A dermoscopic photograph of a skin lesion:
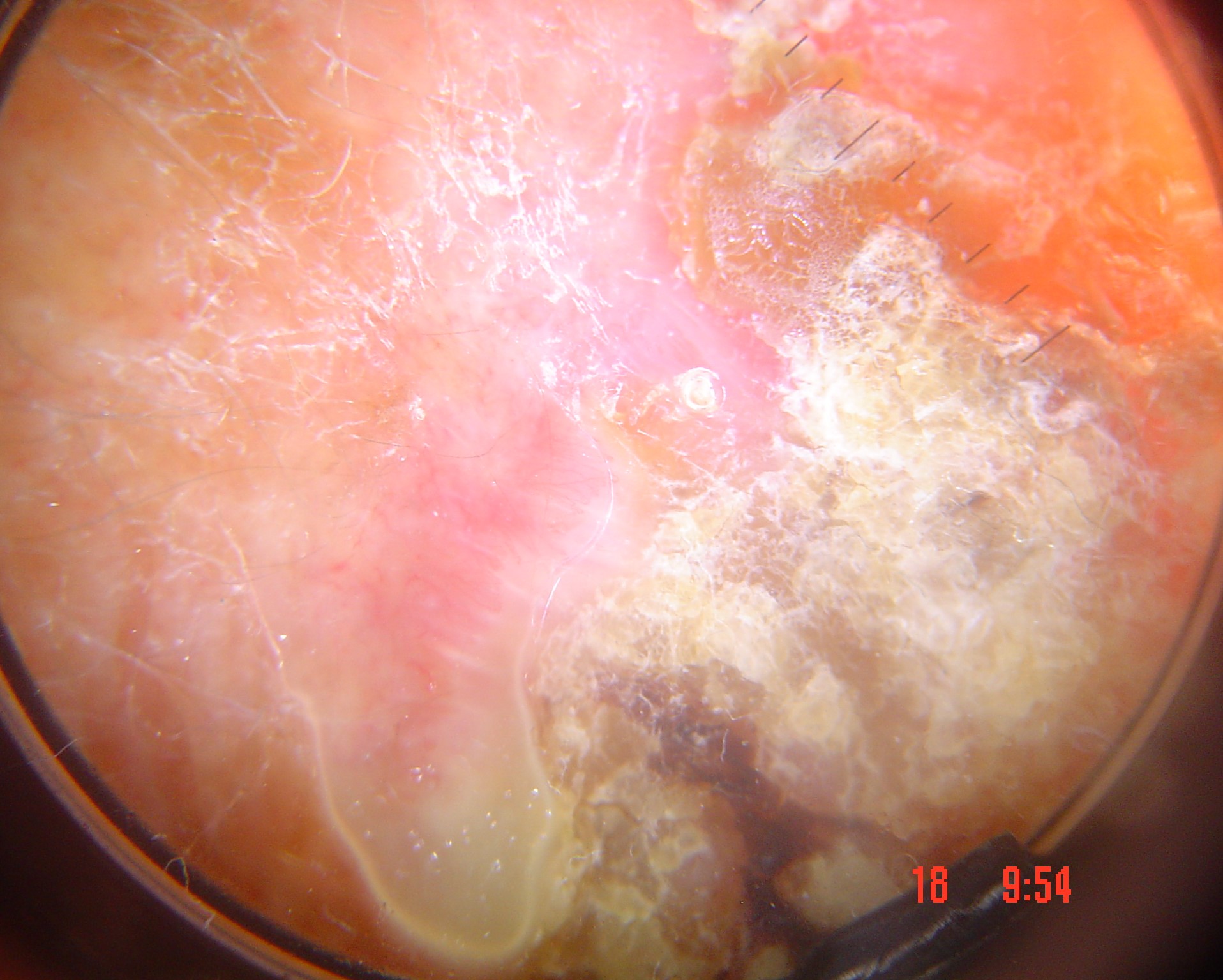Histopathology confirmed a keratinocytic lesion — a squamous cell carcinoma.